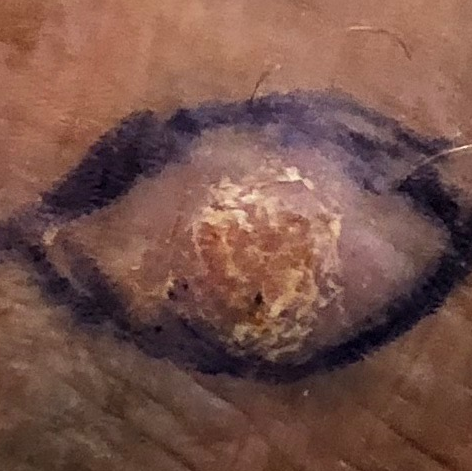A female patient age 60. A smartphone photograph of a skin lesion. The lesion involves a foot. The patient describes that the lesion itches, is elevated, and hurts, but has not changed. Histopathology confirmed an actinic keratosis.